The patient is a male about 25 years old. A dermoscopic image of a skin lesion — 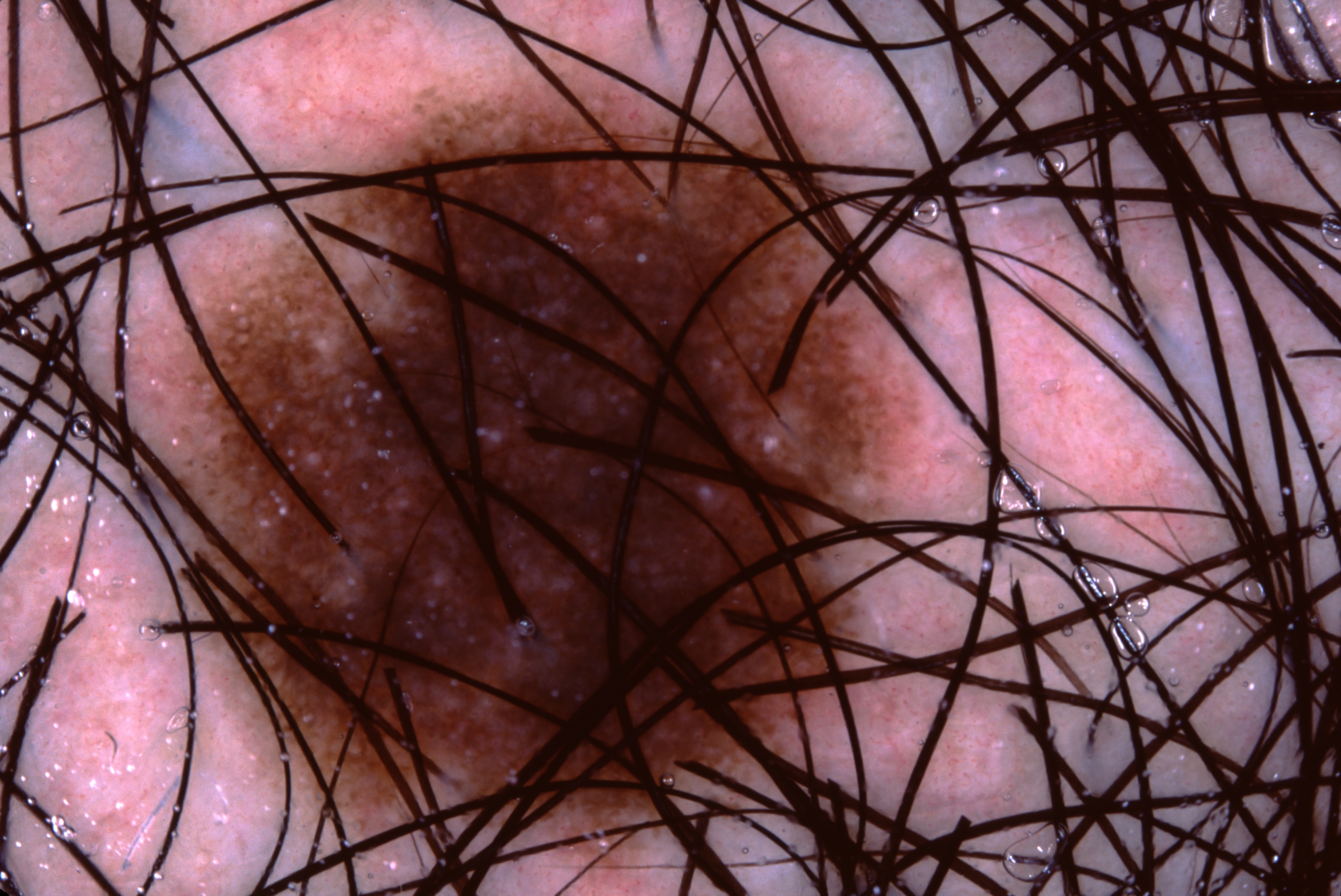bounding box — left=137, top=85, right=936, bottom=863 | dermoscopic features — pigment network | size — large | impression — a melanocytic nevus, a benign lesion.